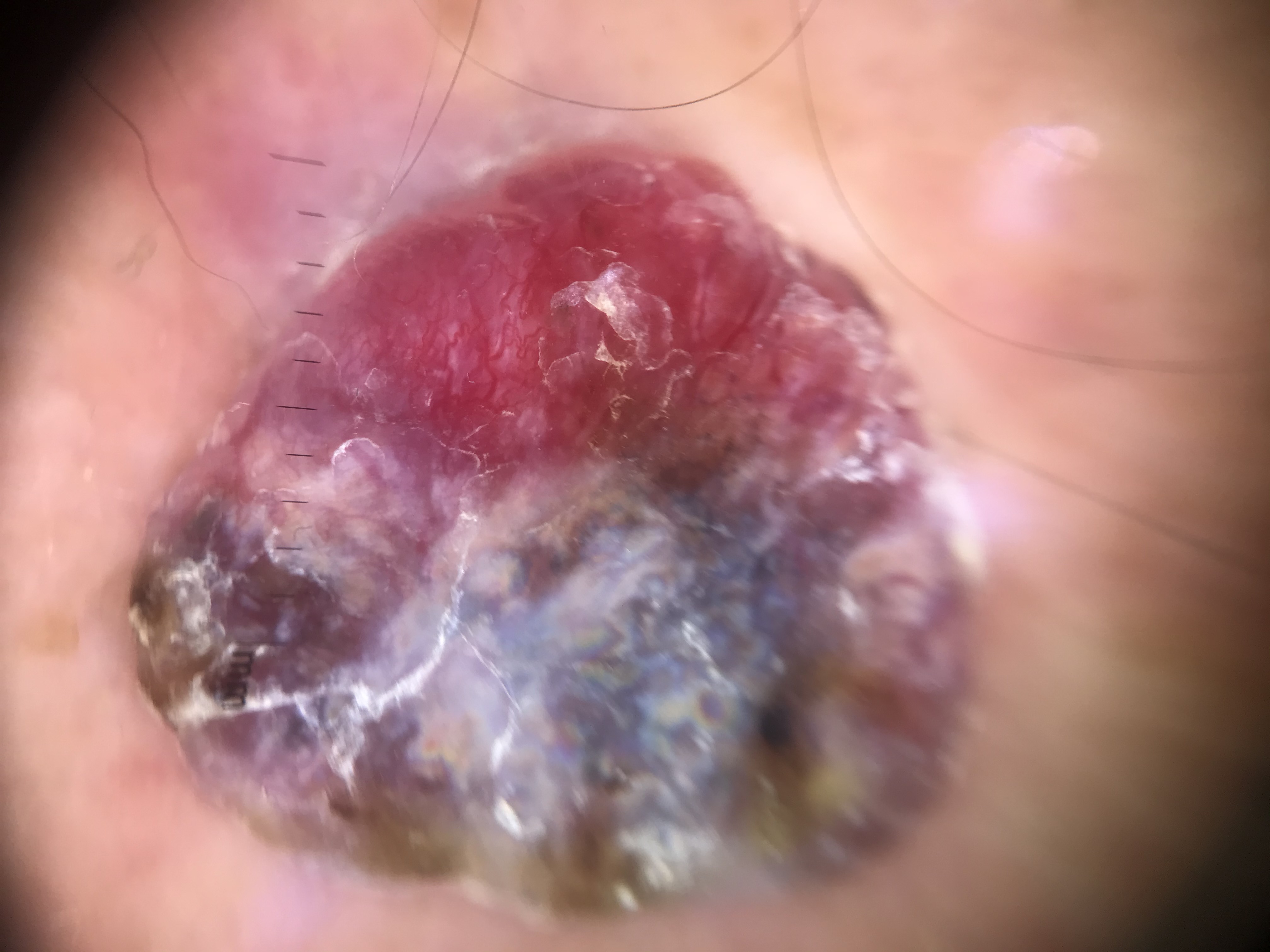Pathology:
The biopsy diagnosis was a melanoma.